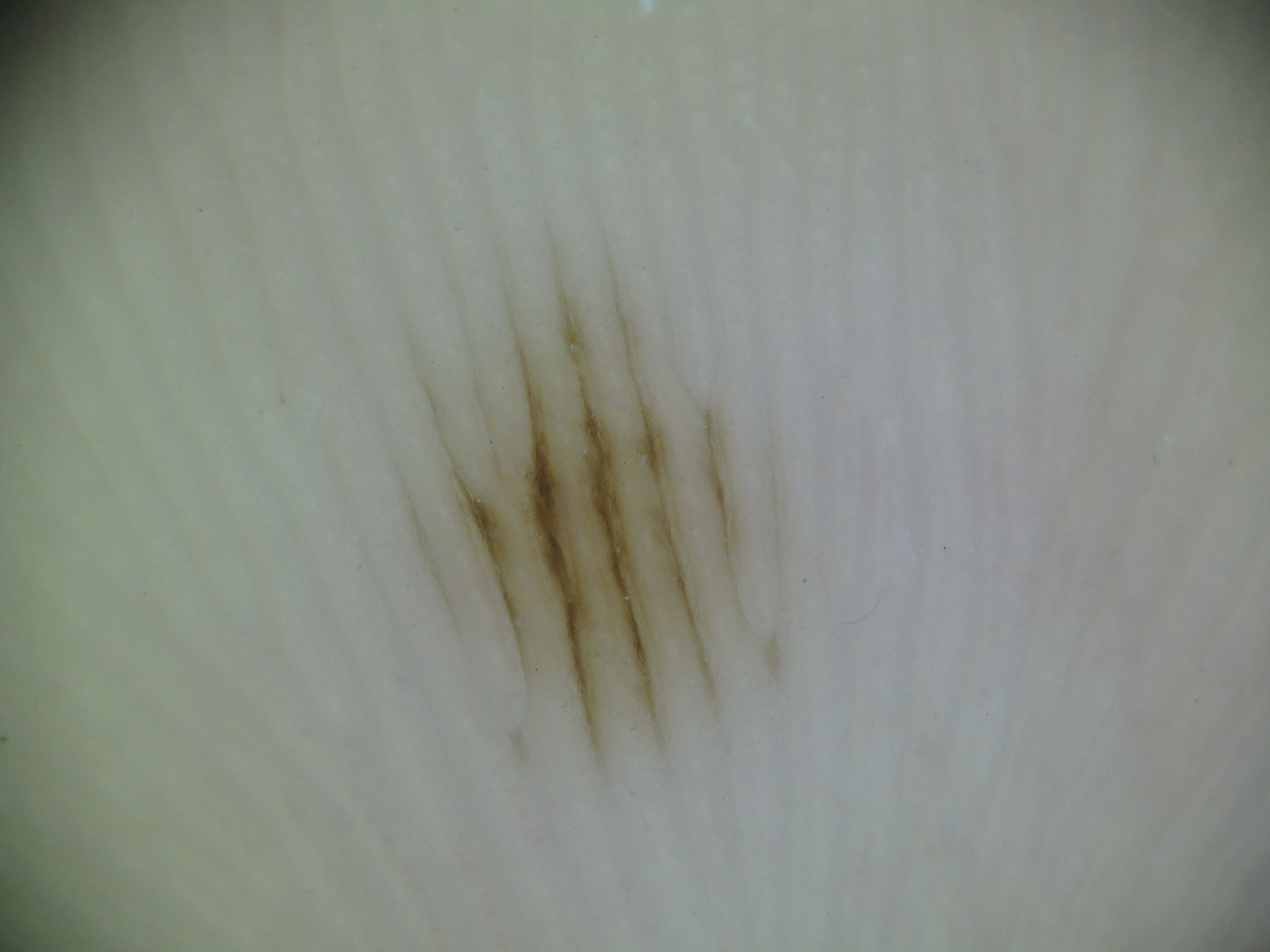Q: What is the diagnosis?
A: acral junctional nevus (expert consensus)